The contributor notes the condition has been present for one to four weeks. The patient is 70–79, male. The affected area is the arm. Self-categorized by the patient as a rash. No relevant systemic symptoms. The contributor notes itching and burning. This is a close-up image. Skin tone: Fitzpatrick III; lay reviewers estimated 2 on the MST.
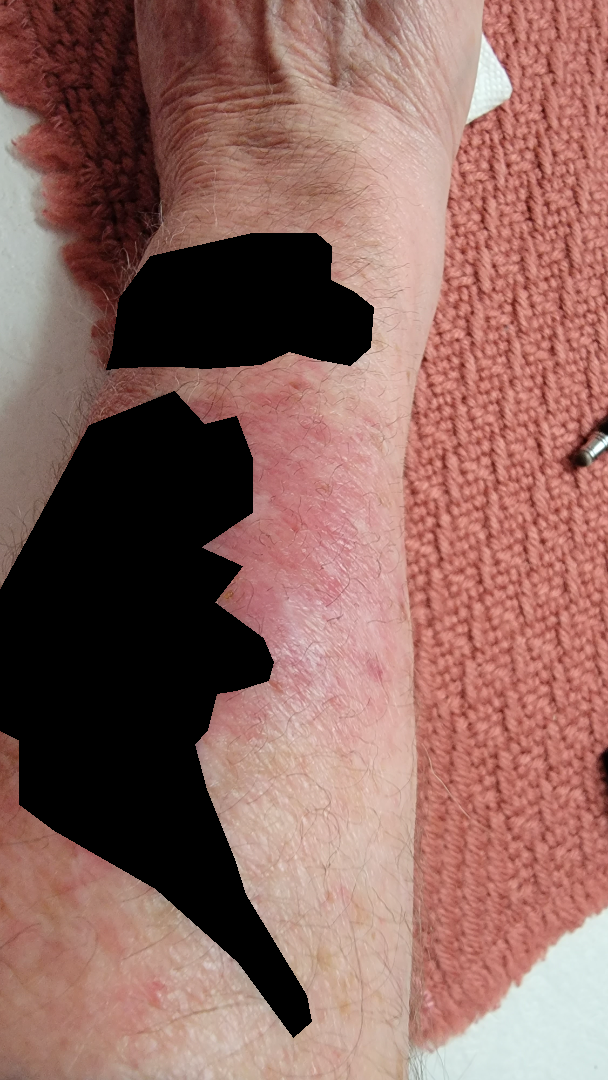On teledermatology review: the reviewer's impression was Eczema.